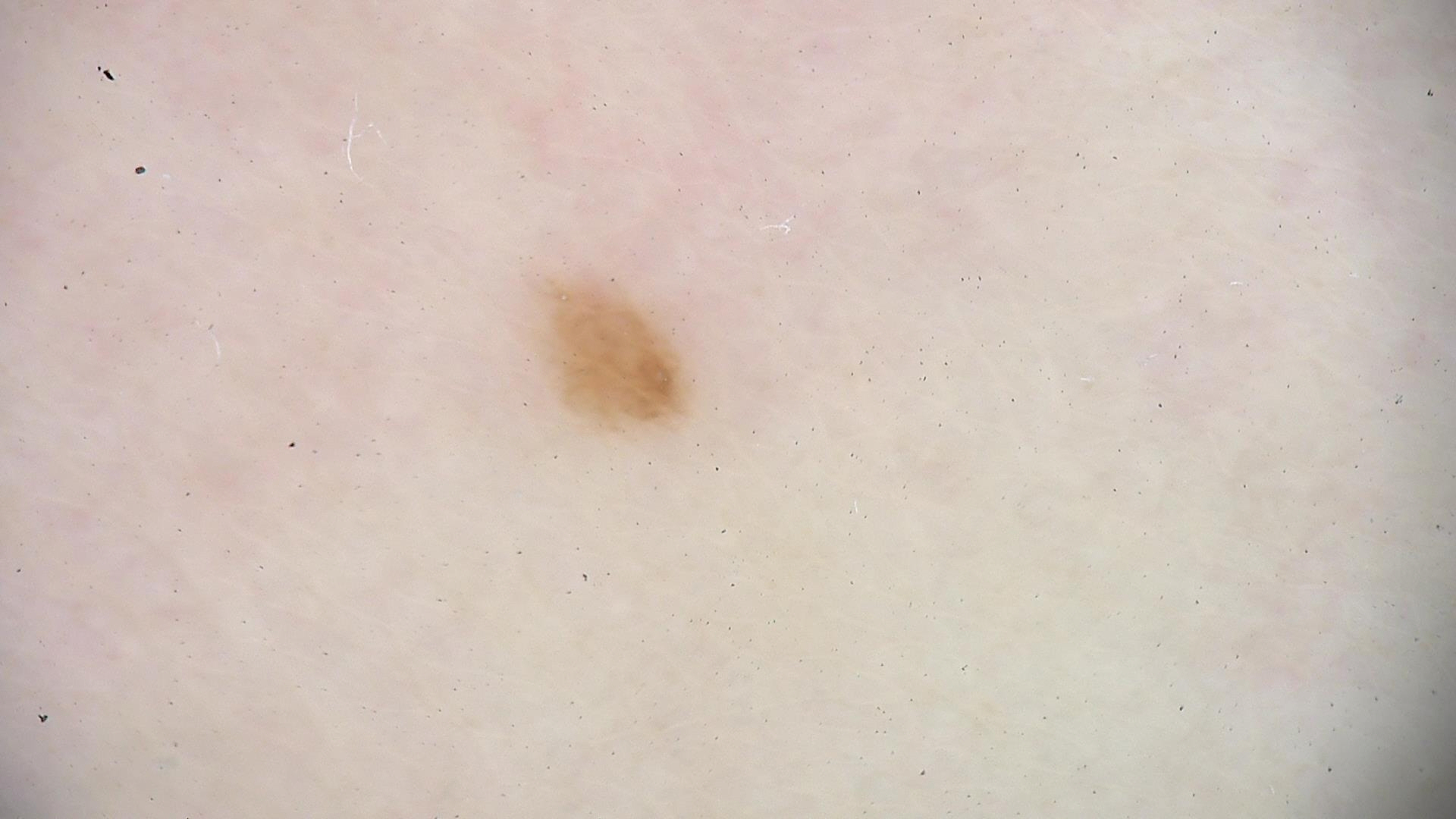Case:
The morphology is that of a banal lesion.
Impression:
The diagnostic label was a junctional nevus.